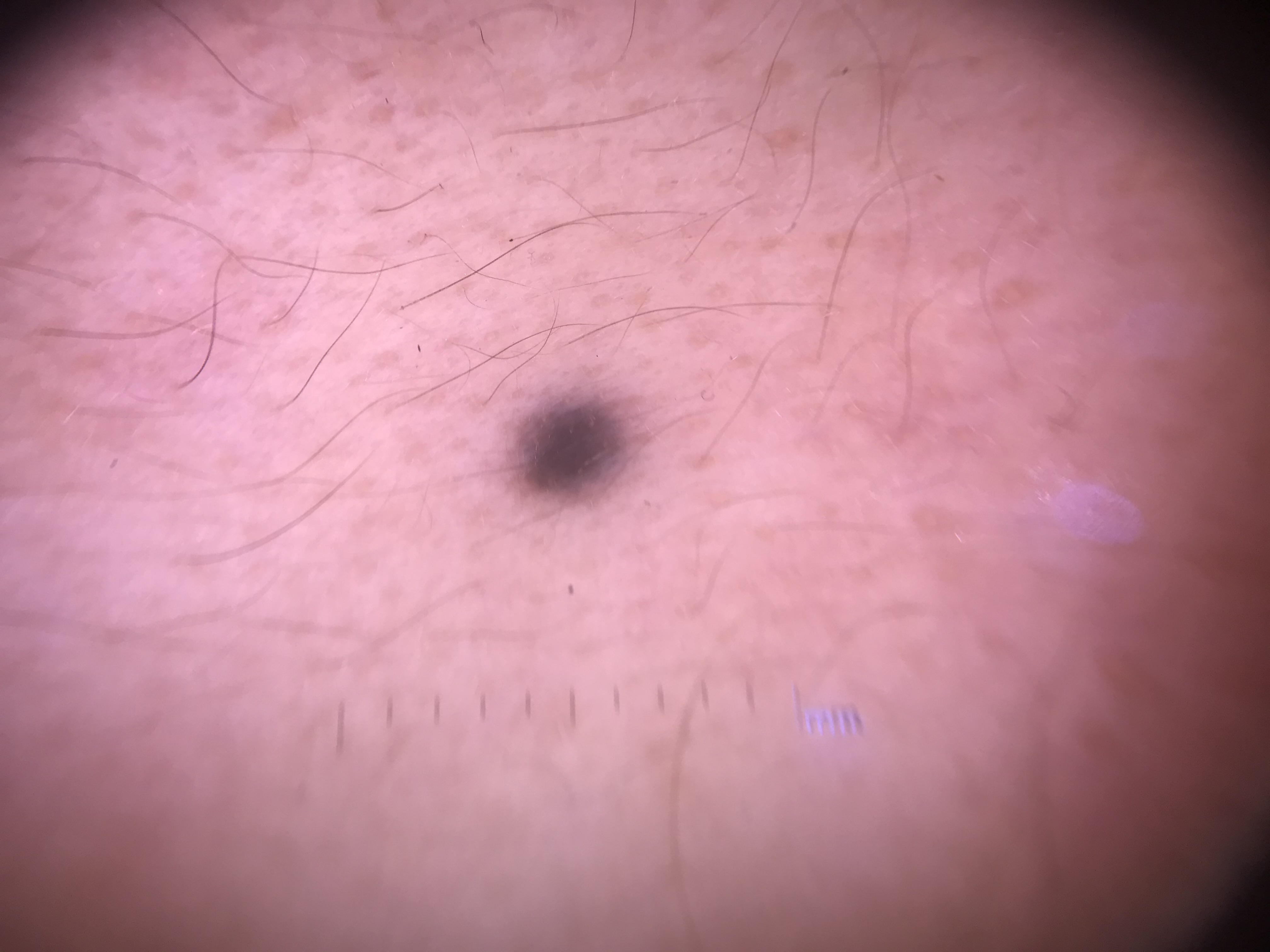Classified as a blue nevus.